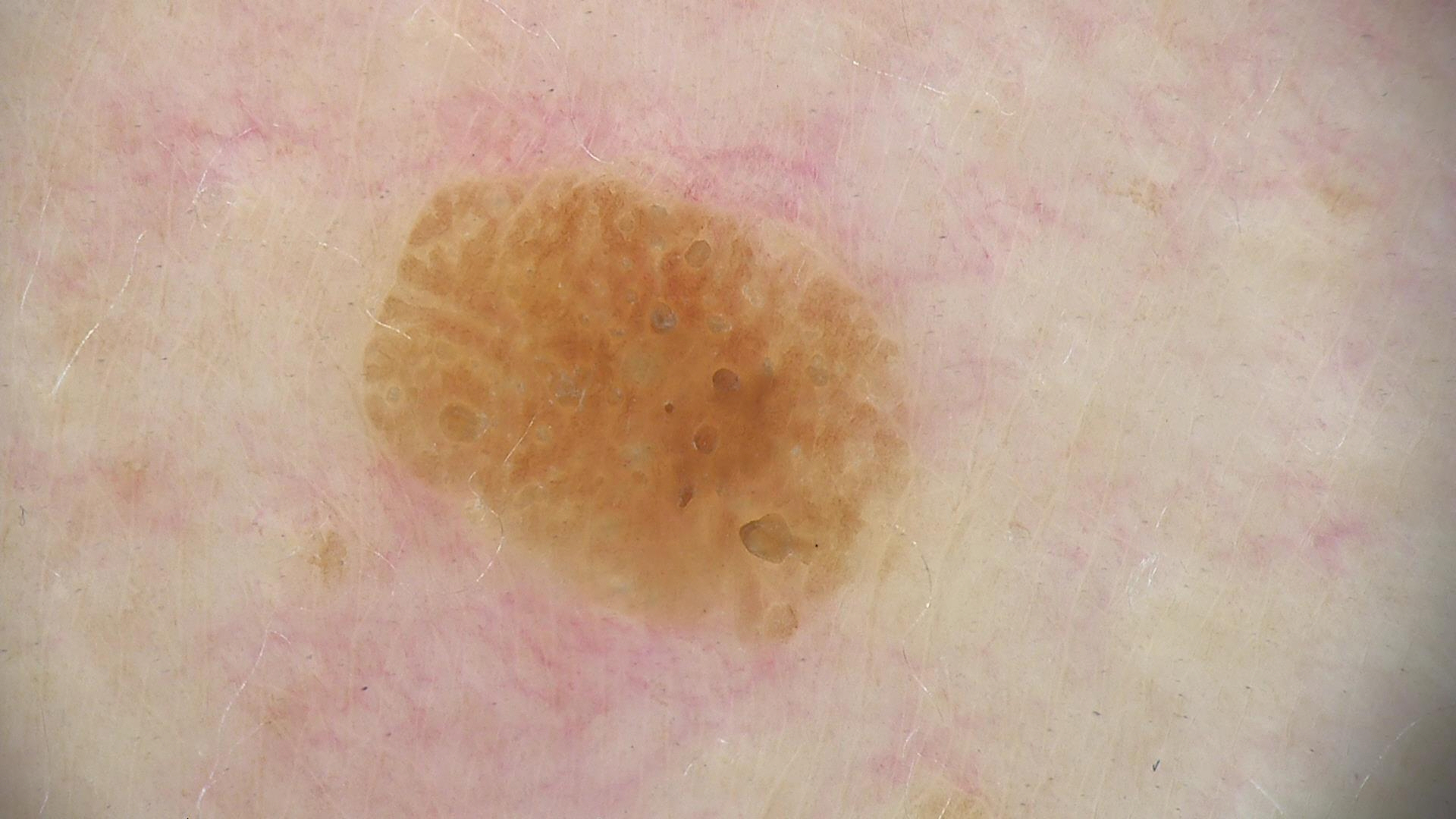Findings:
* imaging: dermoscopy
* subtype: keratinocytic
* label: seborrheic keratosis (expert consensus)